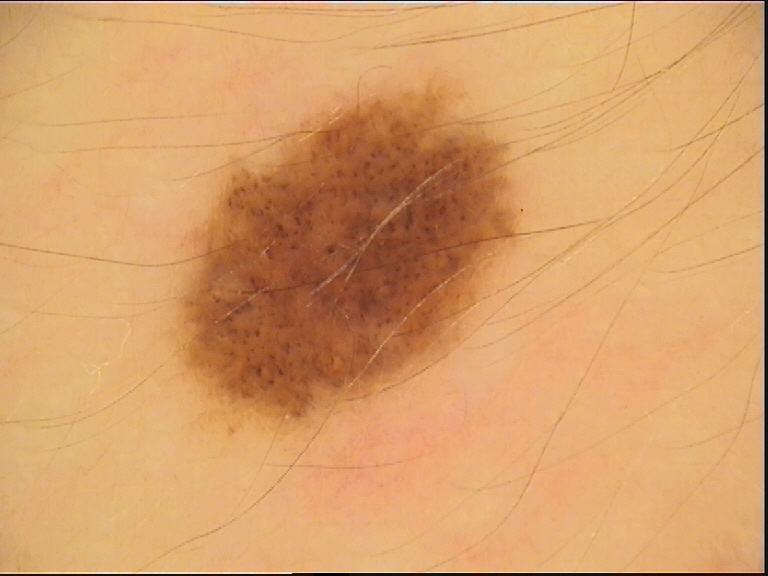Q: What is this lesion?
A: dysplastic junctional nevus (expert consensus)